Dermoscopy of a skin lesion: 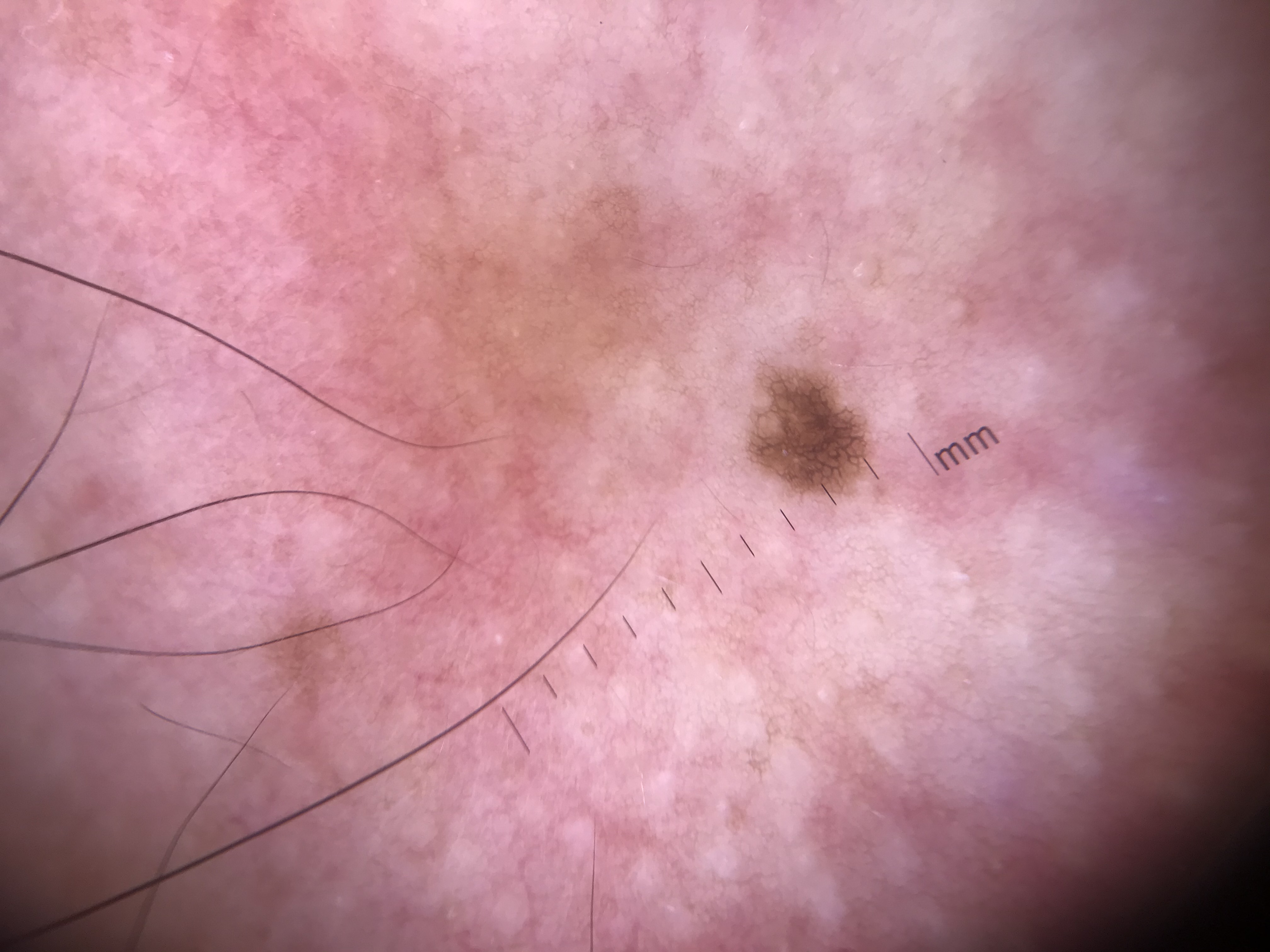Consistent with a banal lesion — a junctional nevus.